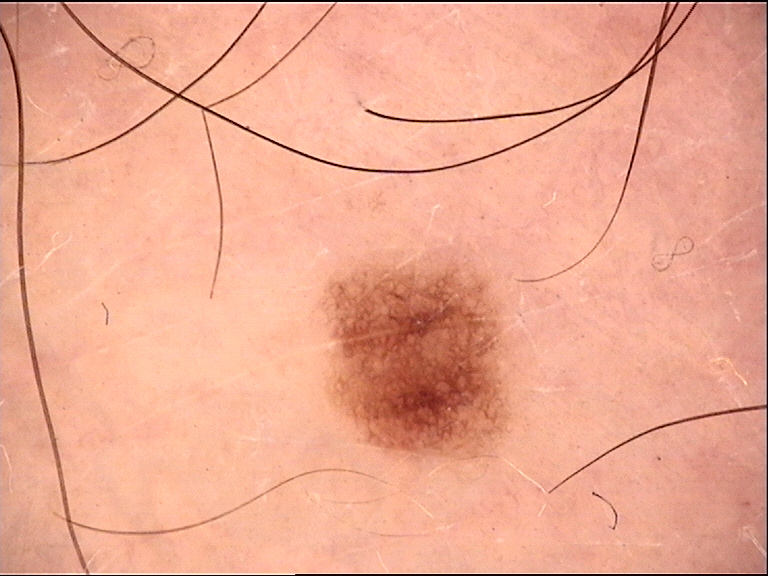diagnosis: dysplastic junctional nevus (expert consensus).